A skin lesion imaged with a dermatoscope.
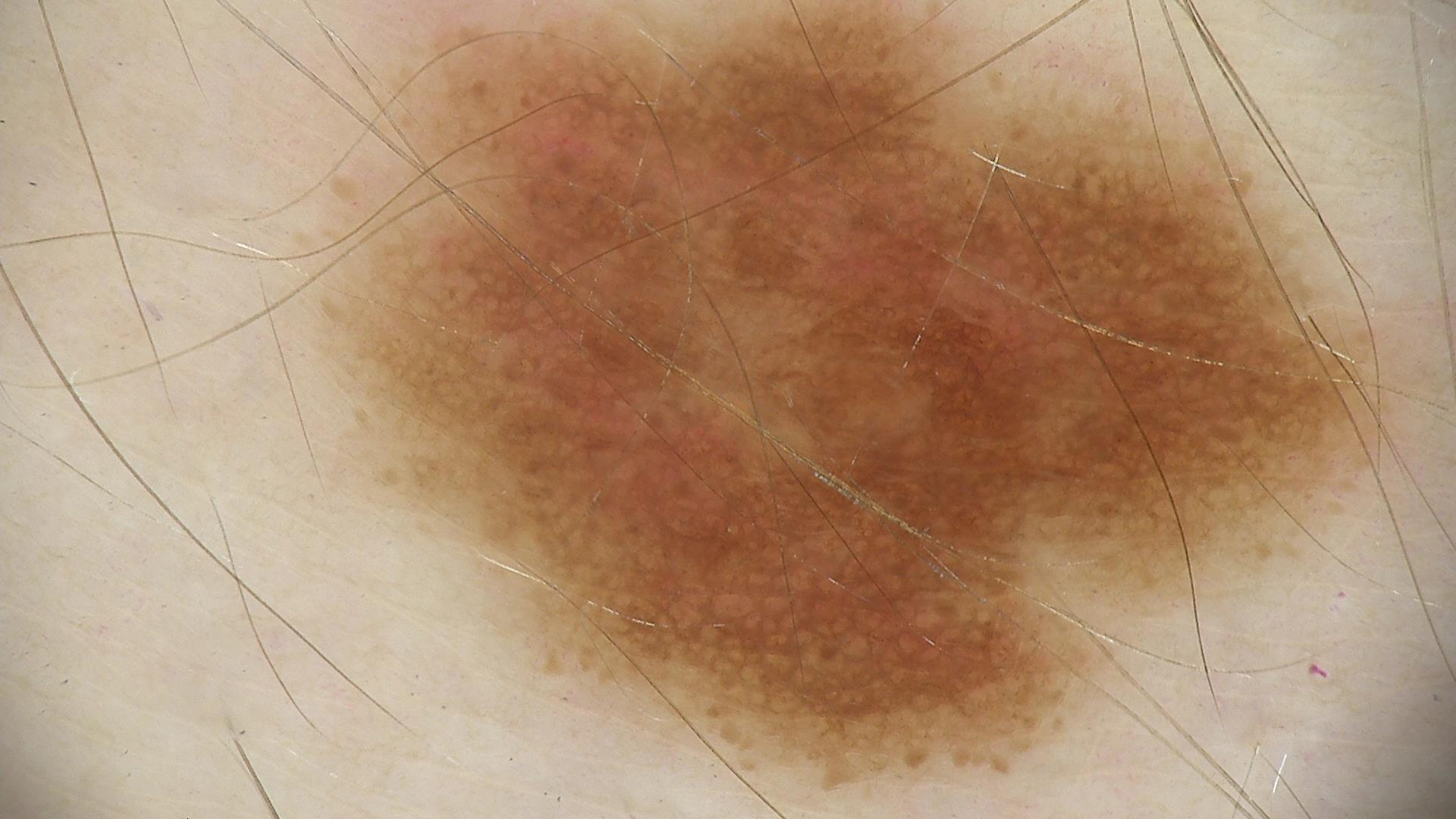Diagnosed as a benign lesion — a dysplastic junctional nevus.